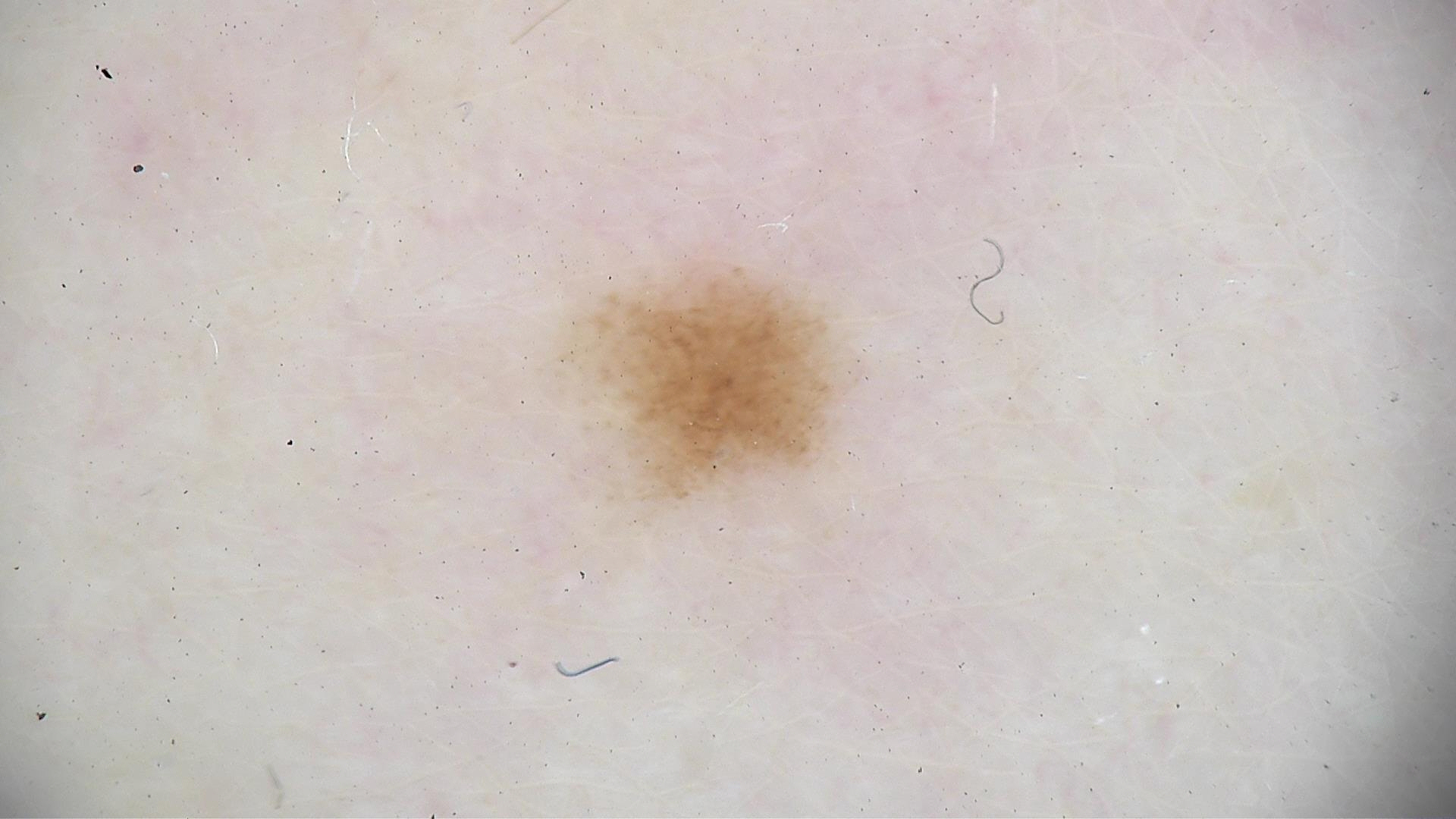diagnosis — dysplastic junctional nevus (expert consensus)